A dermoscopic close-up of a skin lesion:
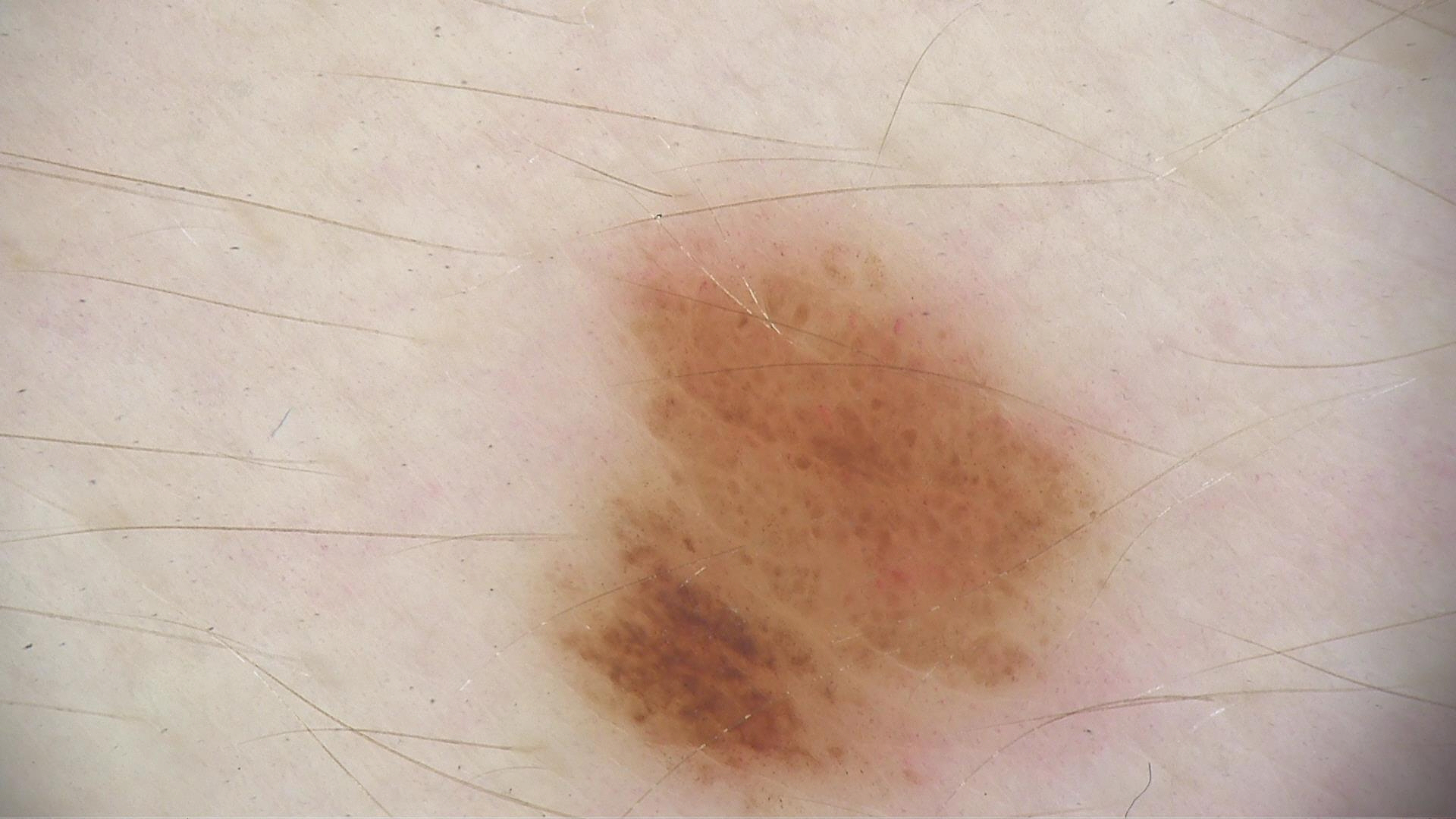Impression:
The diagnostic label was a benign lesion — a dysplastic junctional nevus.